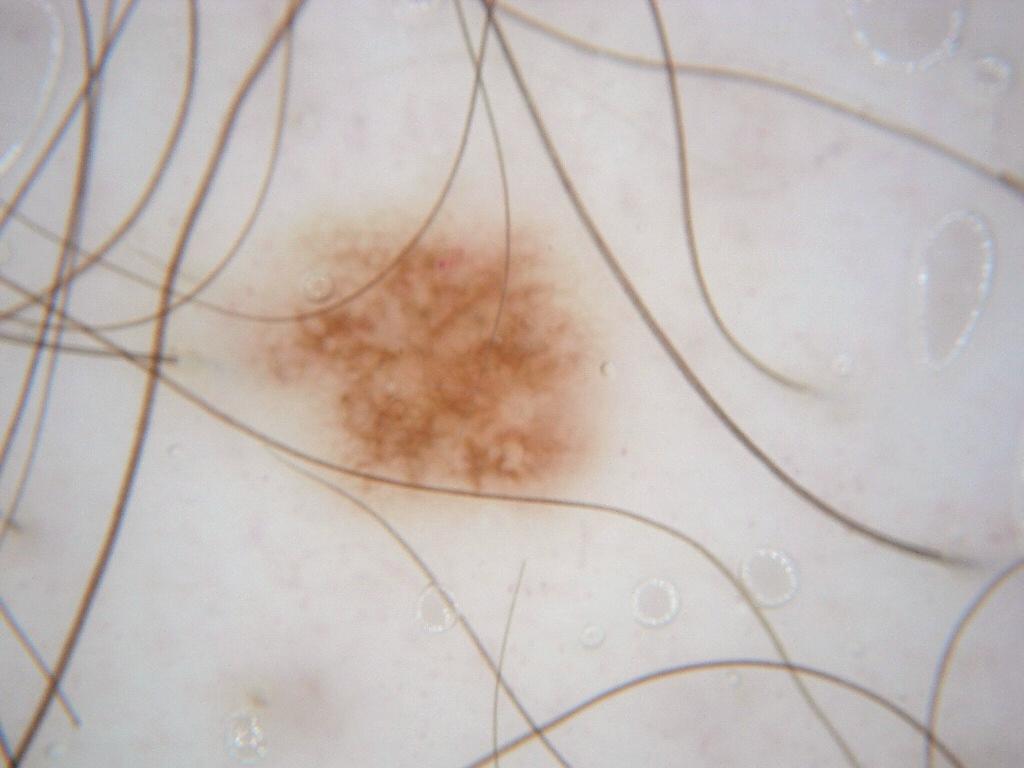A dermoscopy image of a single skin lesion.
In (x1, y1, x2, y2) order, the lesion's extent is bbox=[224, 199, 613, 522].
Consistent with a benign skin lesion.